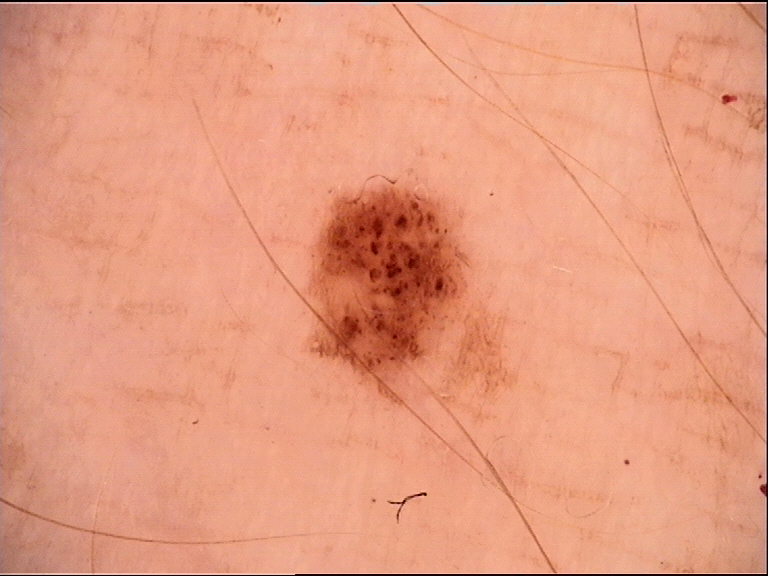A dermoscopic close-up of a skin lesion. Diagnosed as a benign lesion — a dysplastic junctional nevus.